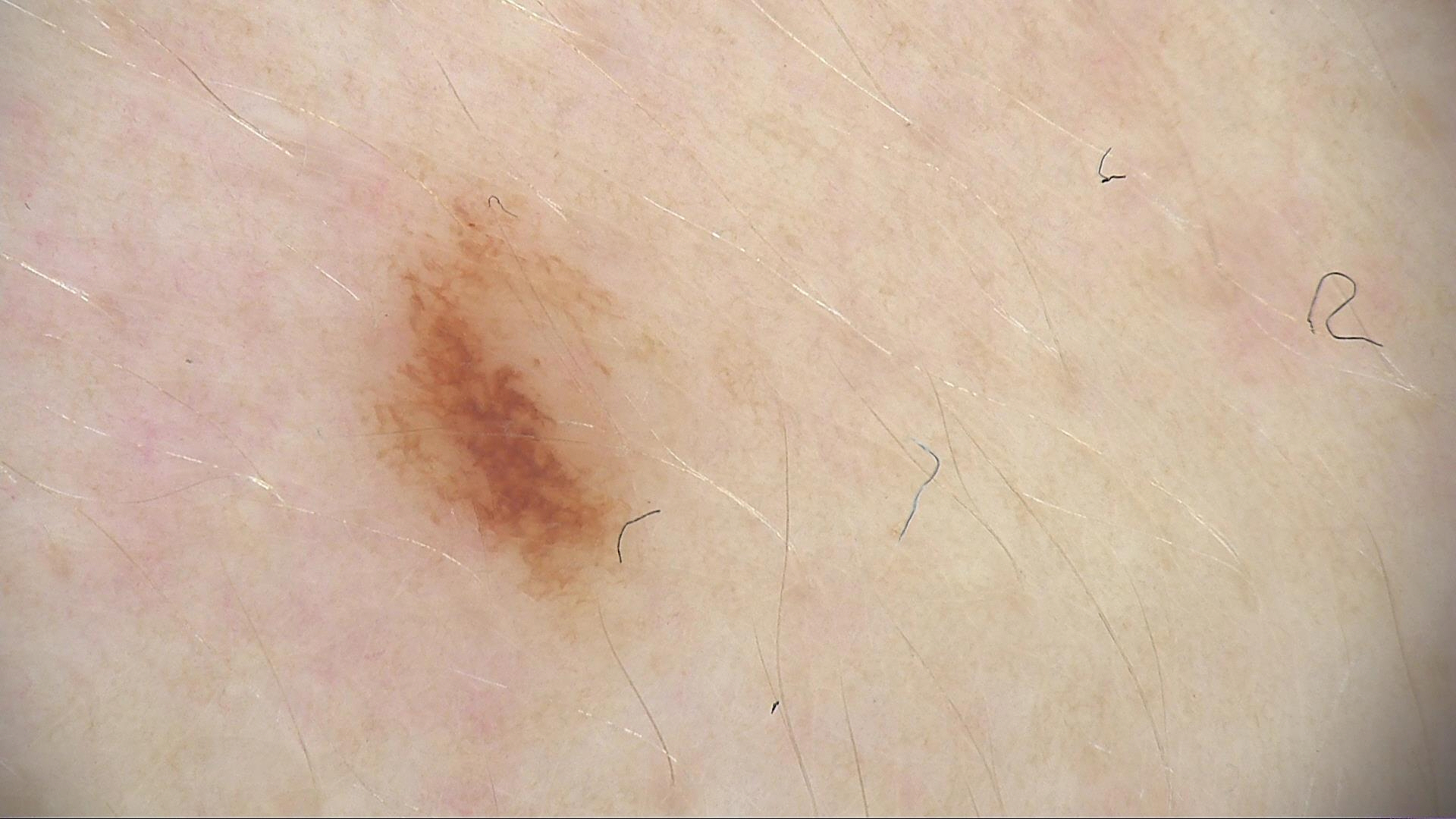class: dysplastic junctional nevus (expert consensus).